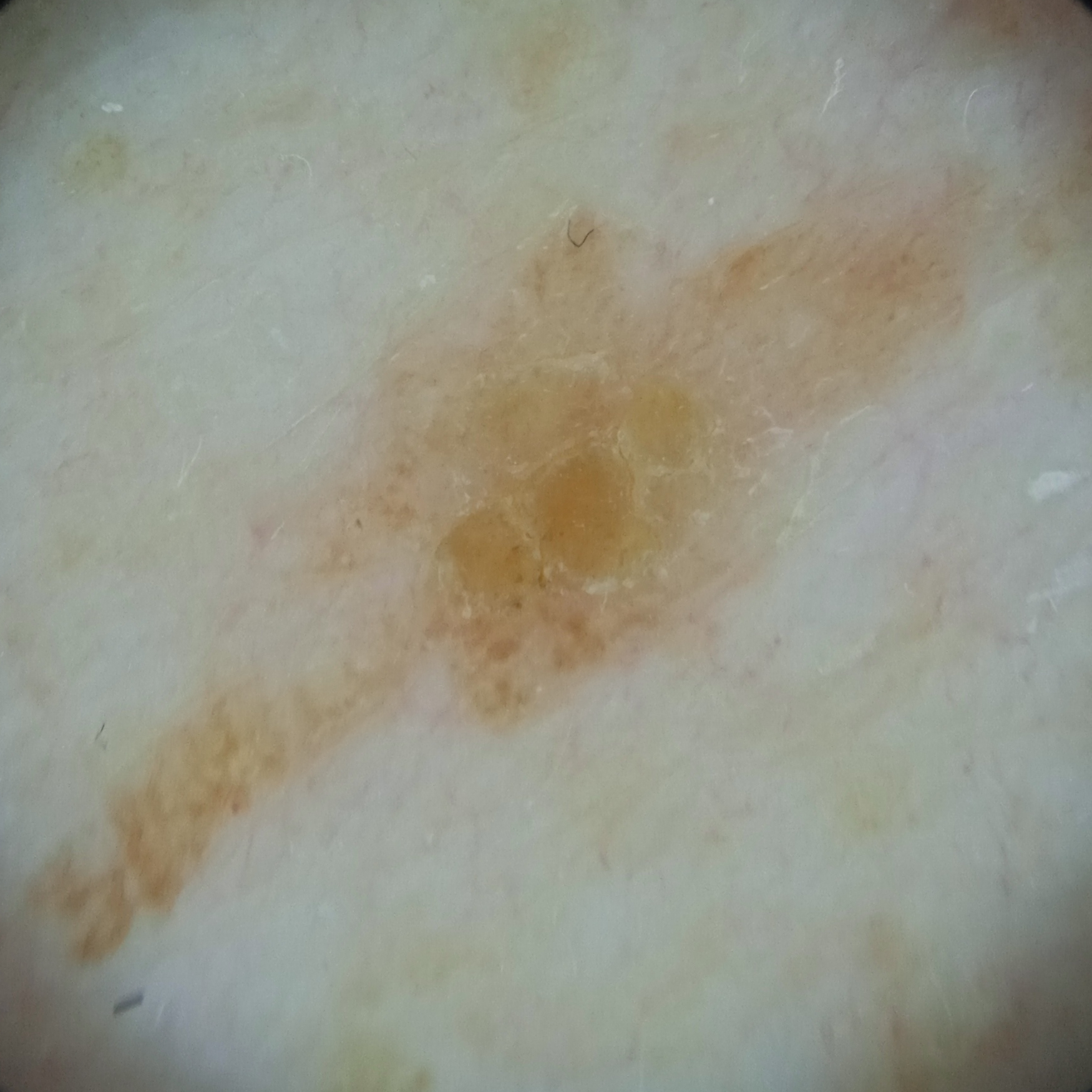Findings:
* sun reaction — skin reddens with sun exposure
* referral — research study (no referral diagnosis)
* size — 16.4 mm
* diagnostic label — seborrheic keratosis (dermatologist consensus)